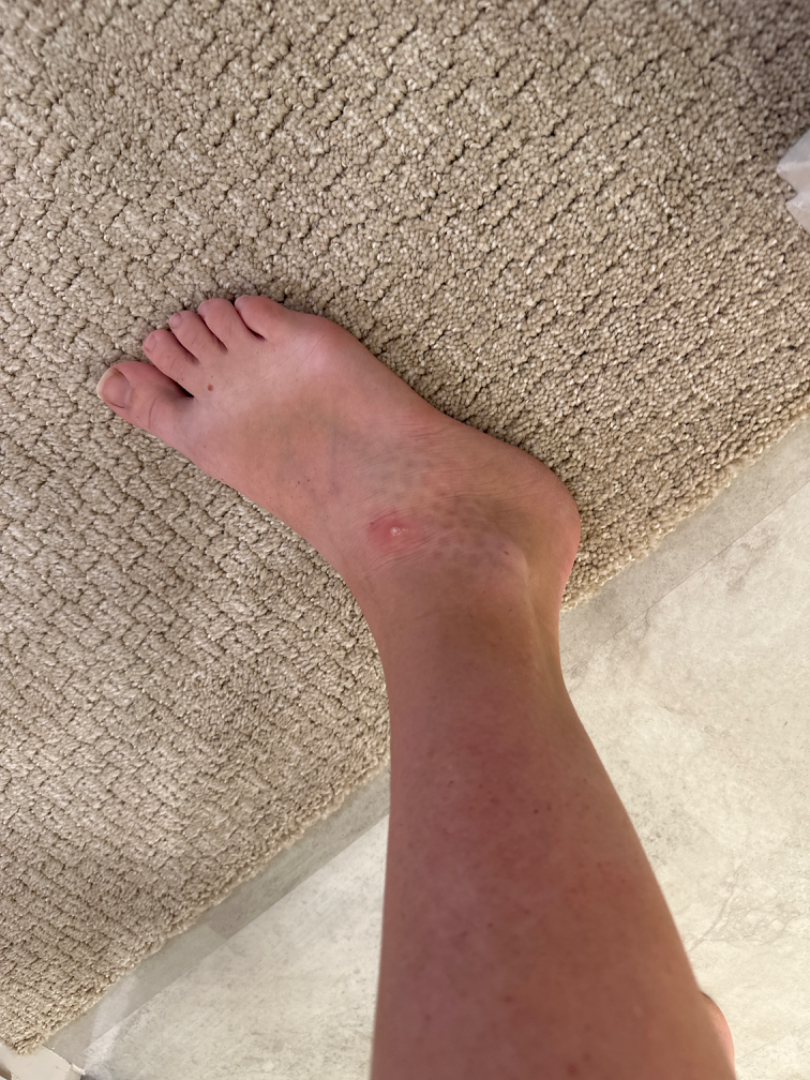impression = one reviewing dermatologist: Clavus and Insect Bite were considered with similar weight